A male subject, aged approximately 15 · a dermatoscopic image of a skin lesion: 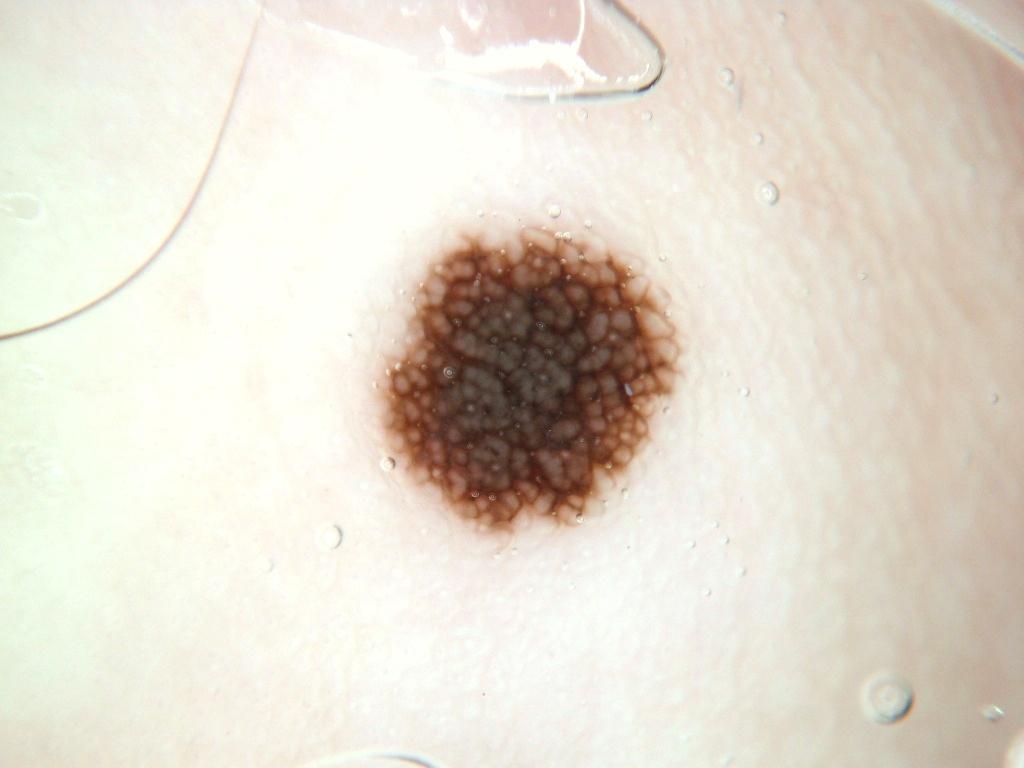<record>
  <lesion_location>
    <bbox_xyxy>374, 224, 681, 538</bbox_xyxy>
  </lesion_location>
  <dermoscopic_features>
    <present>pigment network</present>
    <absent>milia-like cysts, negative network, streaks, globules</absent>
  </dermoscopic_features>
  <diagnosis>
    <name>melanocytic nevus</name>
    <malignancy>benign</malignancy>
    <lineage>melanocytic</lineage>
    <provenance>clinical</provenance>
  </diagnosis>
</record>